By history, prior skin cancer (patient or family) and pesticide exposure · a male subject in their early 50s · FST II · a smartphone photograph of a skin lesion: 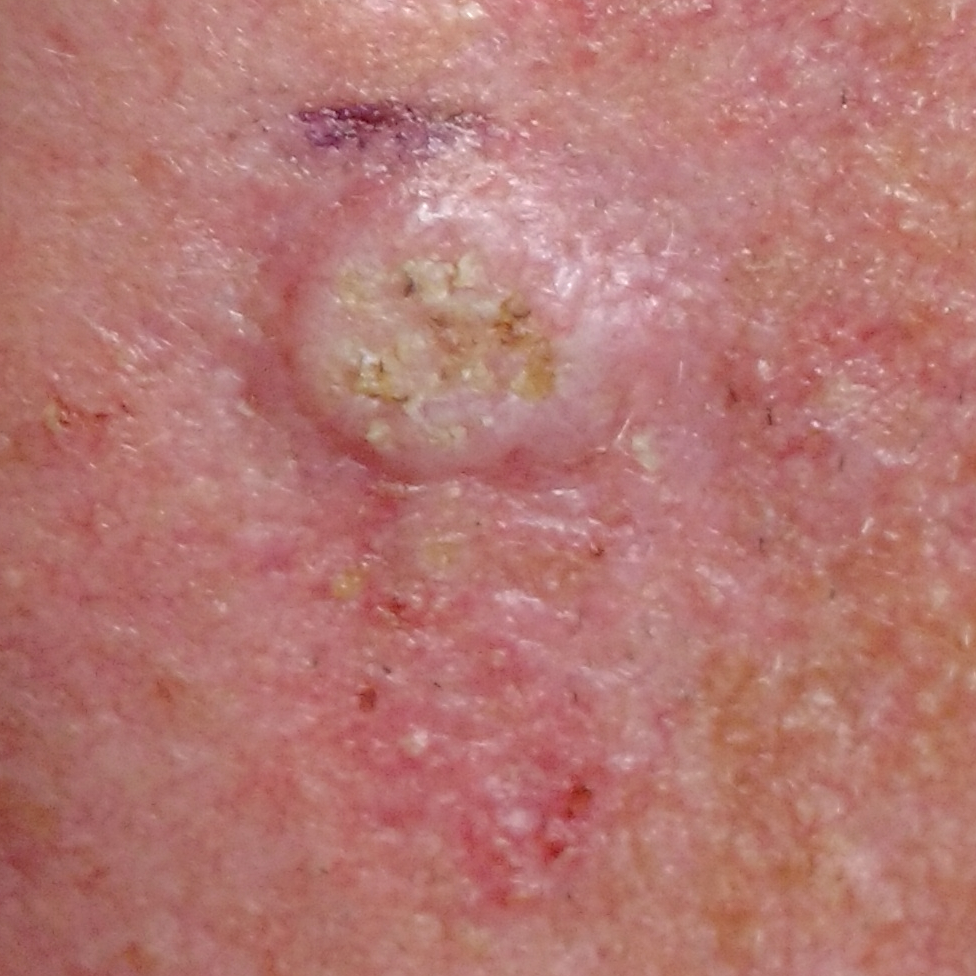site: the face
lesion diameter: 11 × 11 mm
symptoms: itching, elevation / no bleeding
diagnosis: squamous cell carcinoma (biopsy-proven)